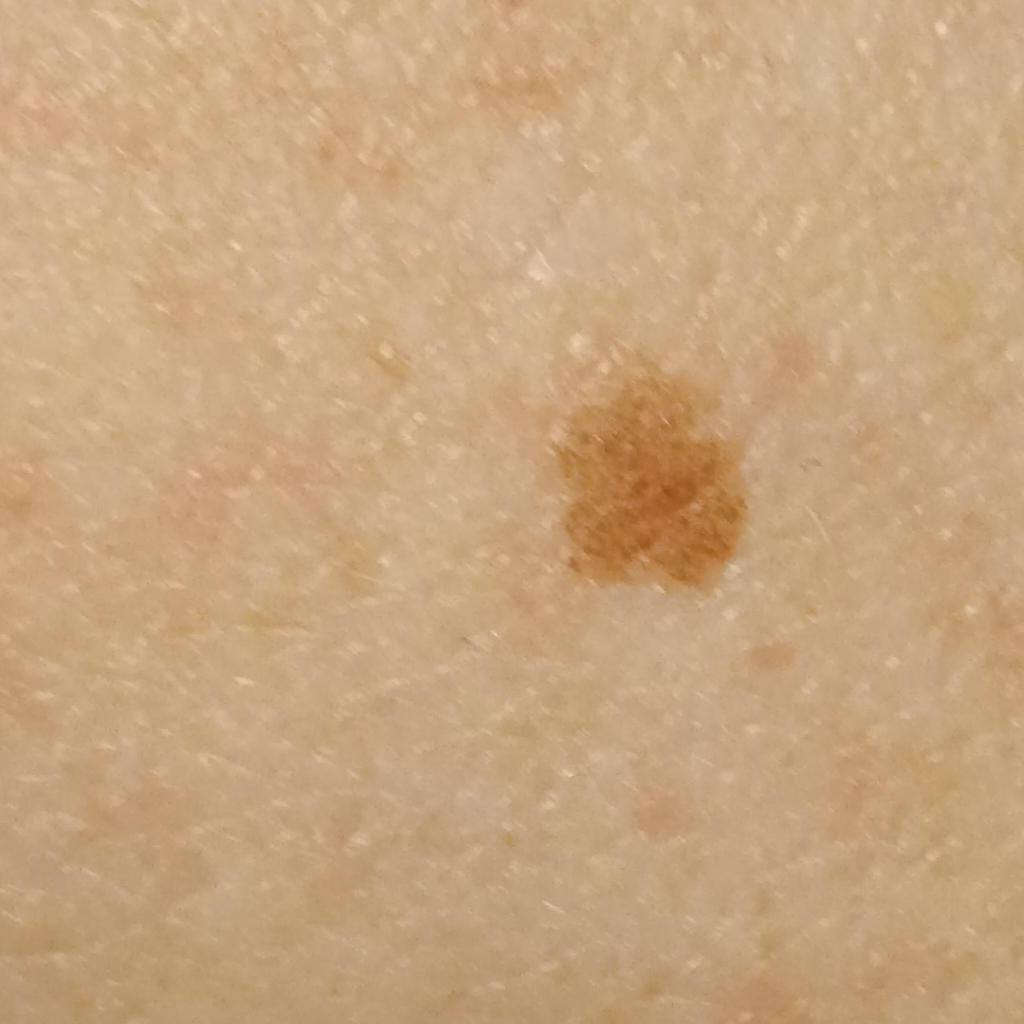• nevus count — a moderate number of melanocytic nevi
• relevant history — a personal history of skin cancer
• image — clinical photograph
• sun reaction — skin reddens with sun exposure
• subject — female, 50 years old
• referral context — research study (no referral diagnosis)
• size — 5.1 mm
• diagnosis — melanocytic nevus (dermatologist consensus)